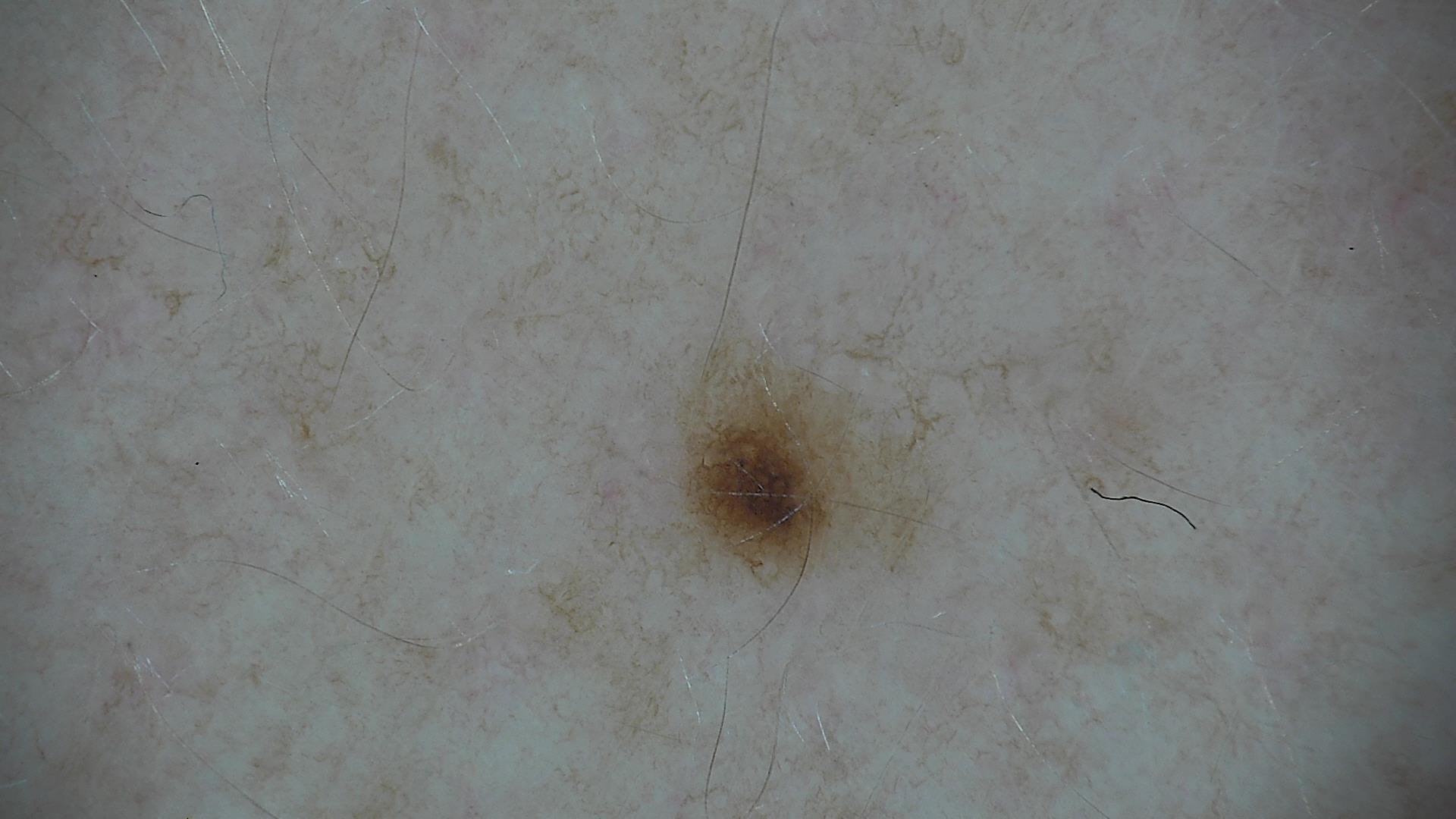A dermoscopic photograph of a skin lesion. The diagnosis was a dysplastic junctional nevus.